Reported duration is three to twelve months; a close-up photograph; the lesion is associated with itching; located on the leg:
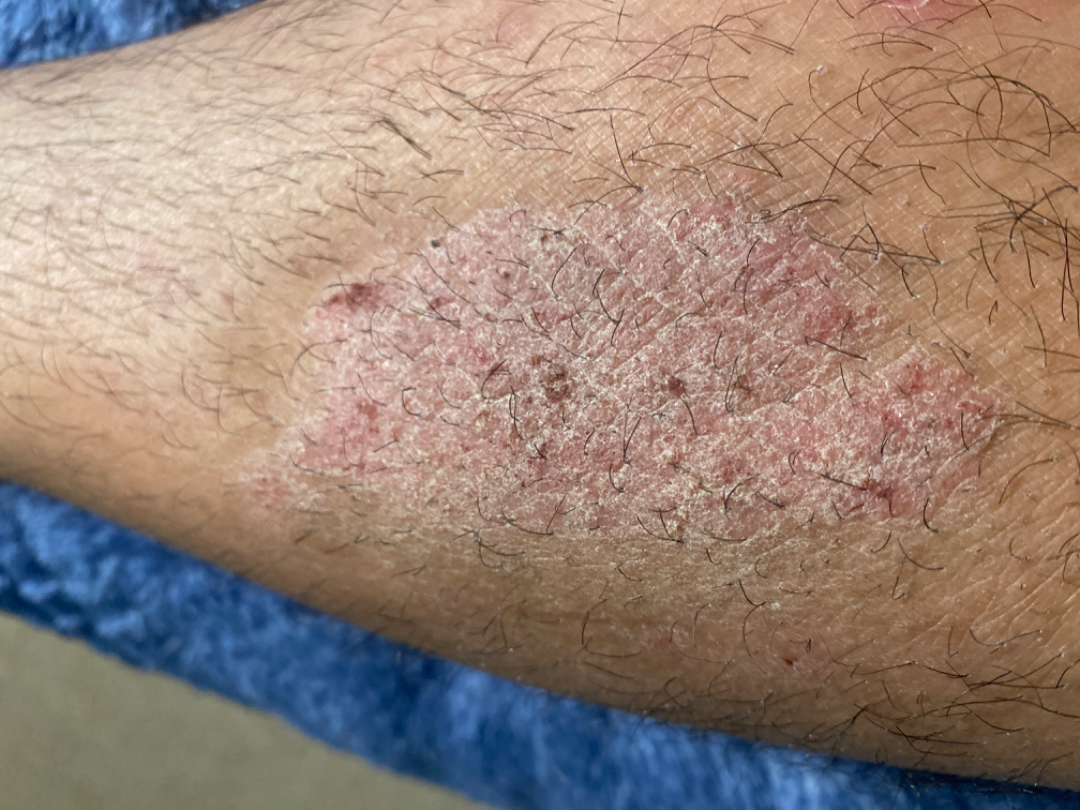Q: What is the dermatologist's impression?
A: Lichen sclerosus (0.50); Psoriasis (0.50)